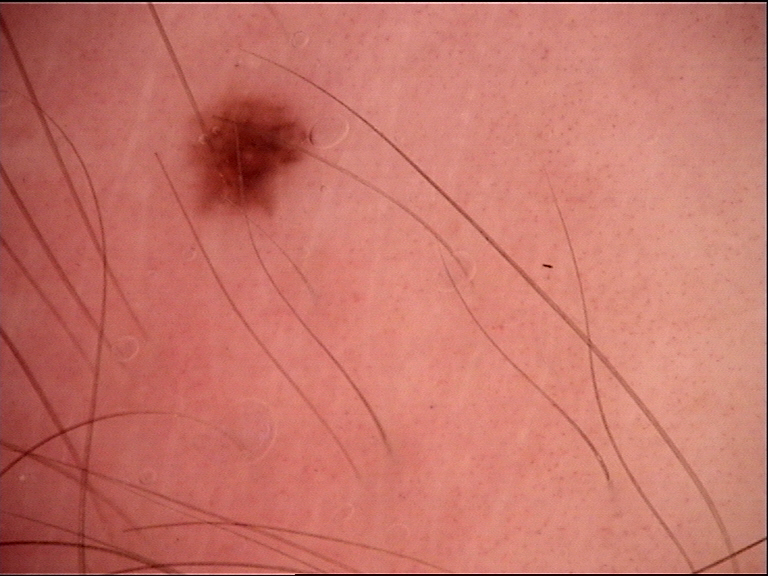diagnosis — dysplastic junctional nevus (expert consensus).